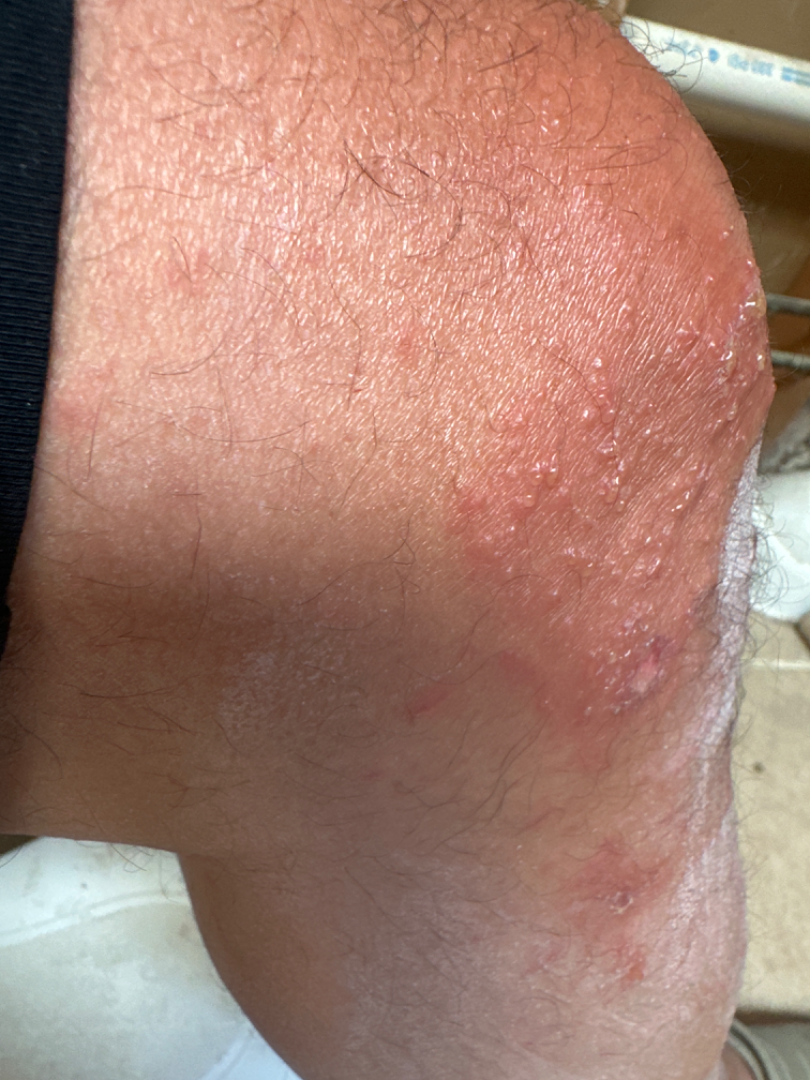The lesion involves the top or side of the foot, head or neck, leg, arm and back of the torso. The photograph was taken at an angle. On dermatologist assessment of the image, Impetigo (possible); Psoriasis (possible); Allergic Contact Dermatitis (possible).